This is a dermoscopic photograph of a skin lesion, the patient is a female about 60 years old.
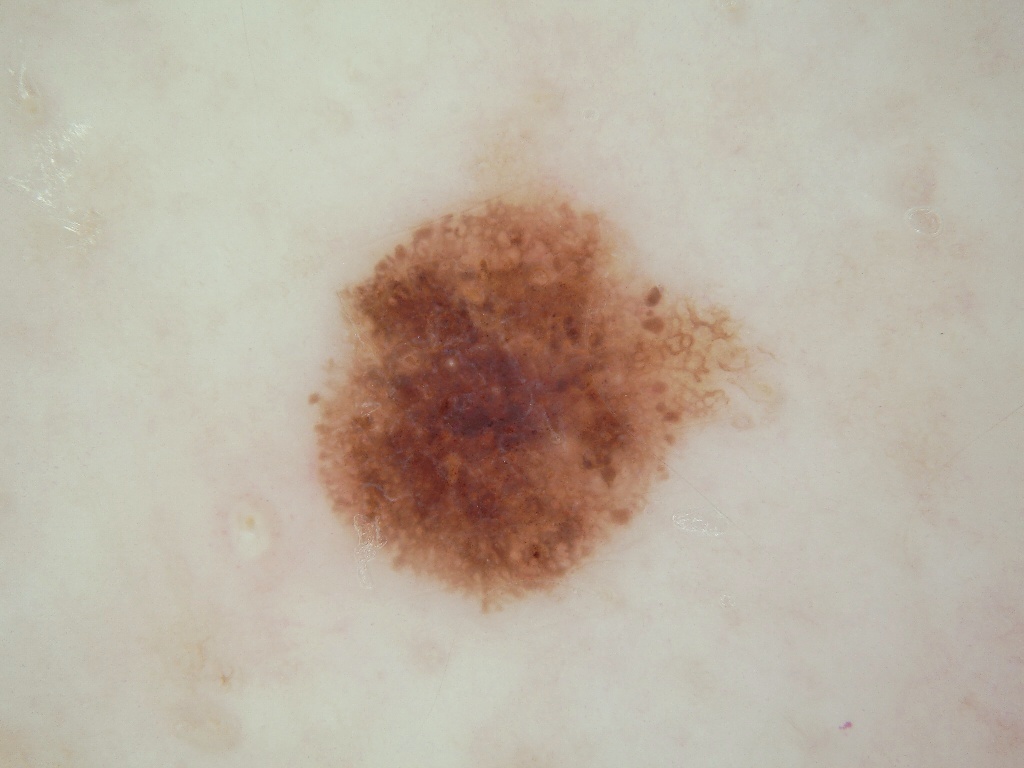Image and clinical context: Dermoscopy demonstrates pigment network, milia-like cysts, and globules. As (left, top, right, bottom), the lesion is located at (304, 153, 781, 614). Impression: The diagnostic assessment was a melanocytic nevus, a benign lesion.